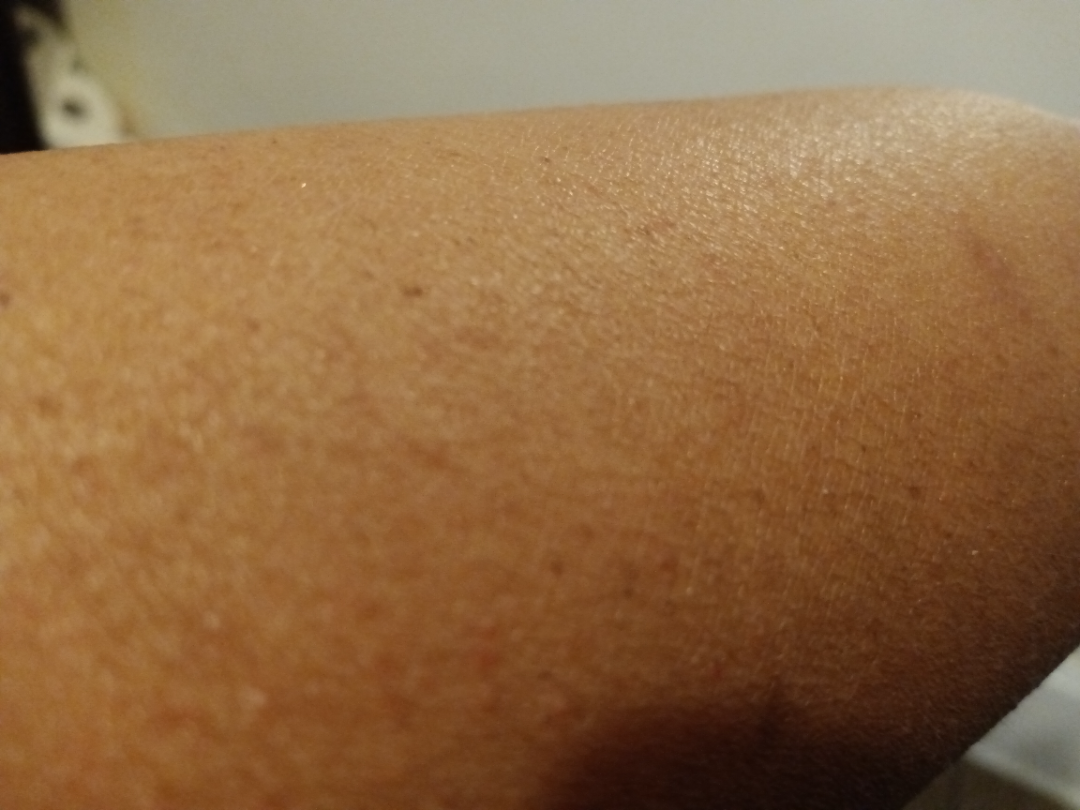No discernible skin pathology was identified on dermatologist review.
A close-up photograph.